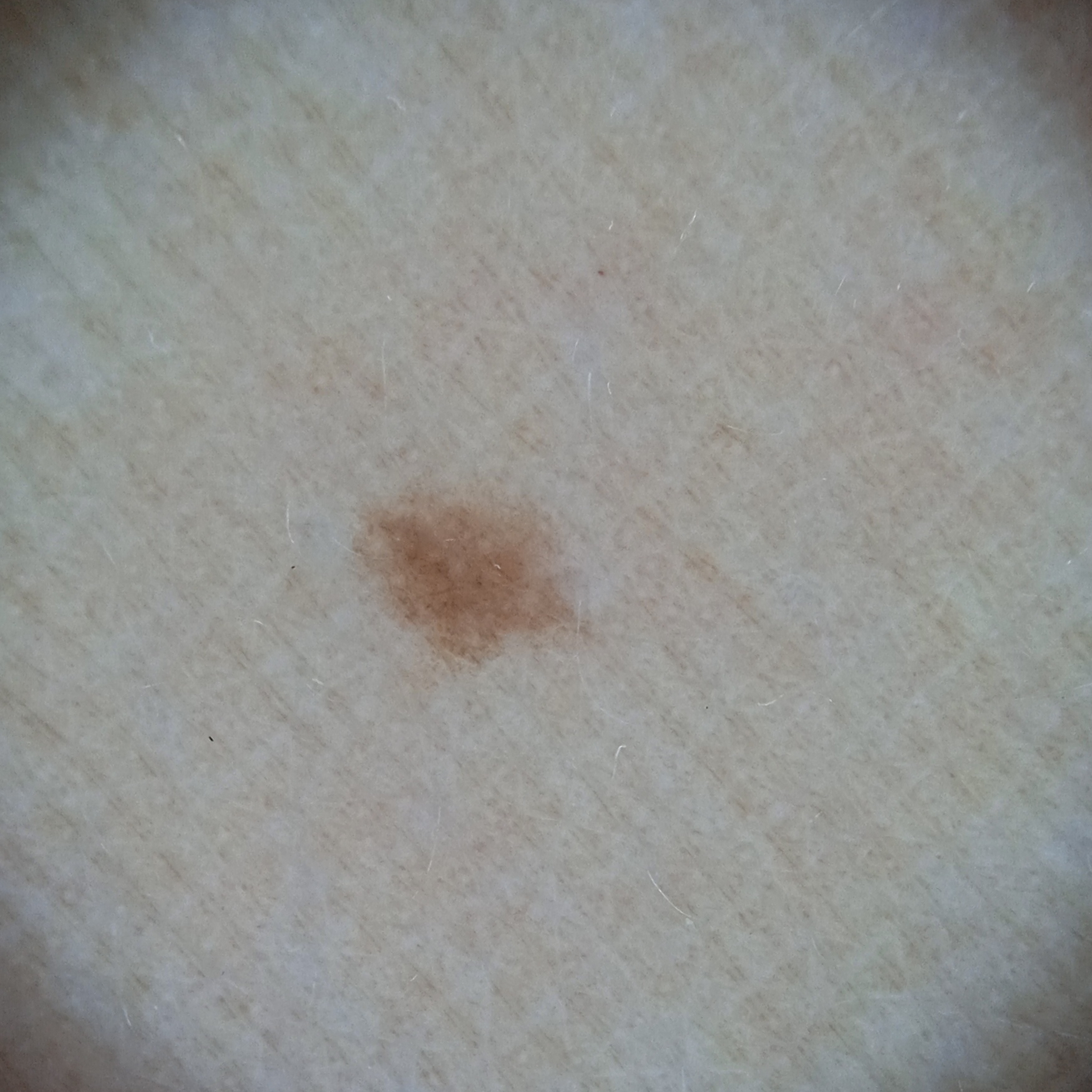patient = female, age 47; sun reaction = skin tans without first burning; risk factors = a history of sunbed use, no personal history of cancer; referral = research study (no referral diagnosis); nevus count = a moderate number of melanocytic nevi; imaging = dermoscopic image; location = an arm; lesion size = 2.7 mm; diagnostic label = melanocytic nevus (dermatologist consensus).